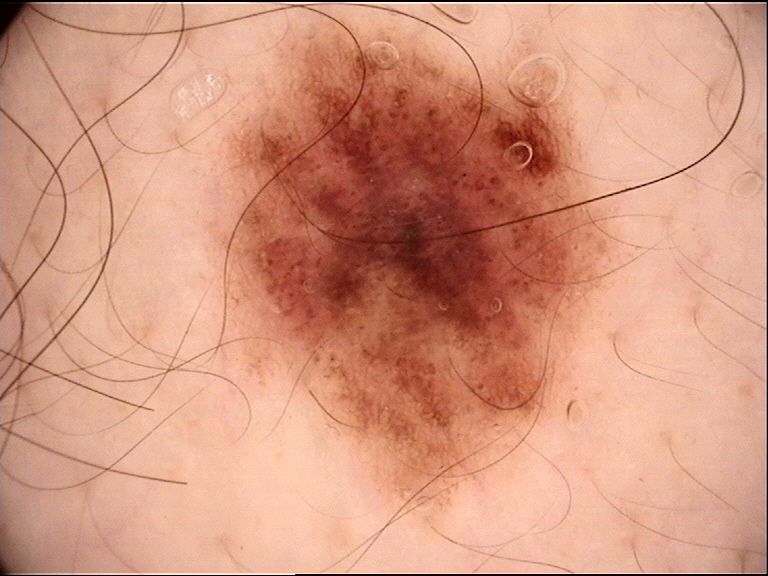imaging: dermoscopy; assessment: dysplastic compound nevus (expert consensus).